The patient describes having a moderate number of moles. A clinical photograph showing a skin lesion. The patient says their skin tans without first burning. Acquired for a research image collection, with no referral diagnosis. A male subject age 72:
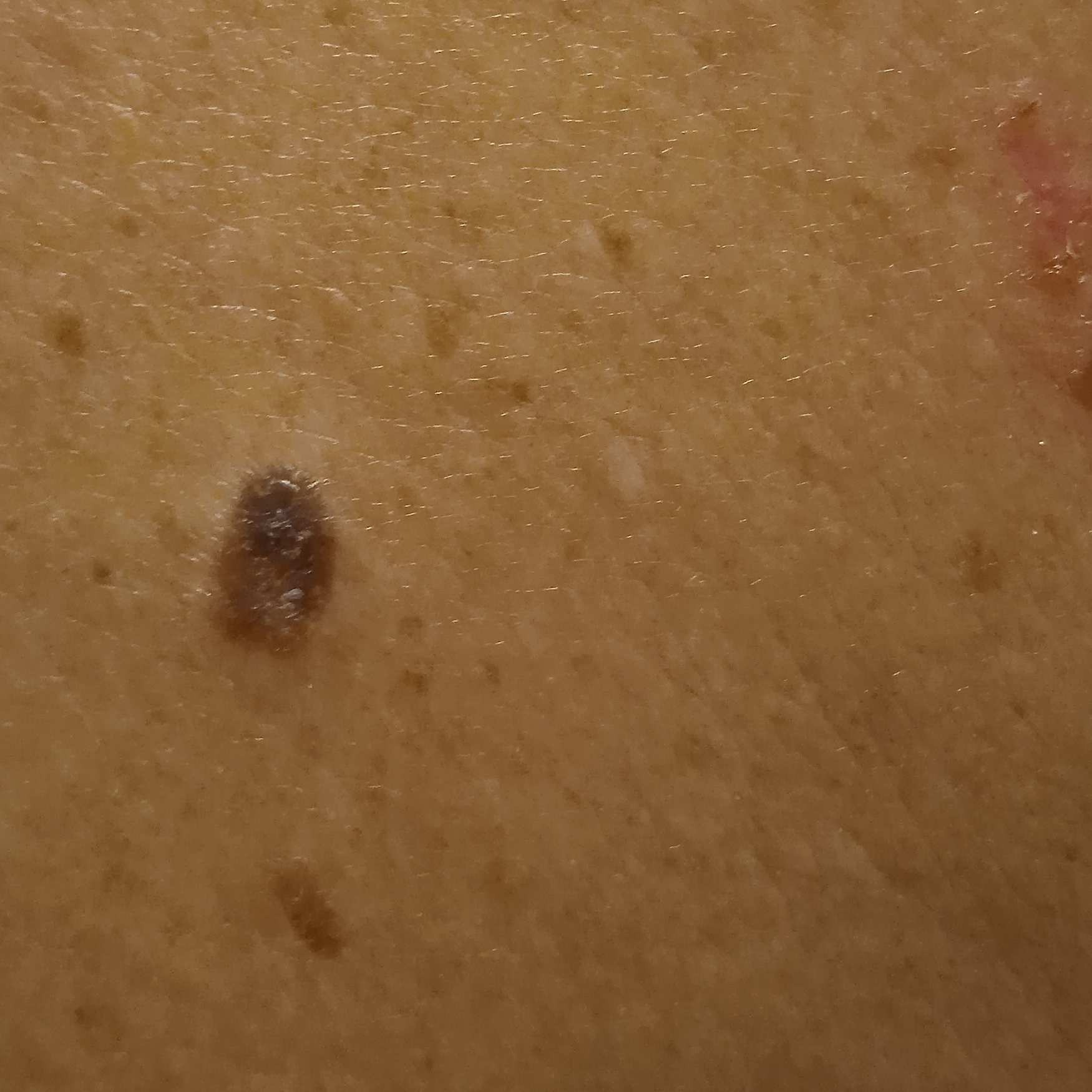The lesion involves the back.
The lesion is about 8.1 mm across.
The dermatologists' assessment was a seborrheic keratosis.